The lesion involves the leg, an image taken at a distance — 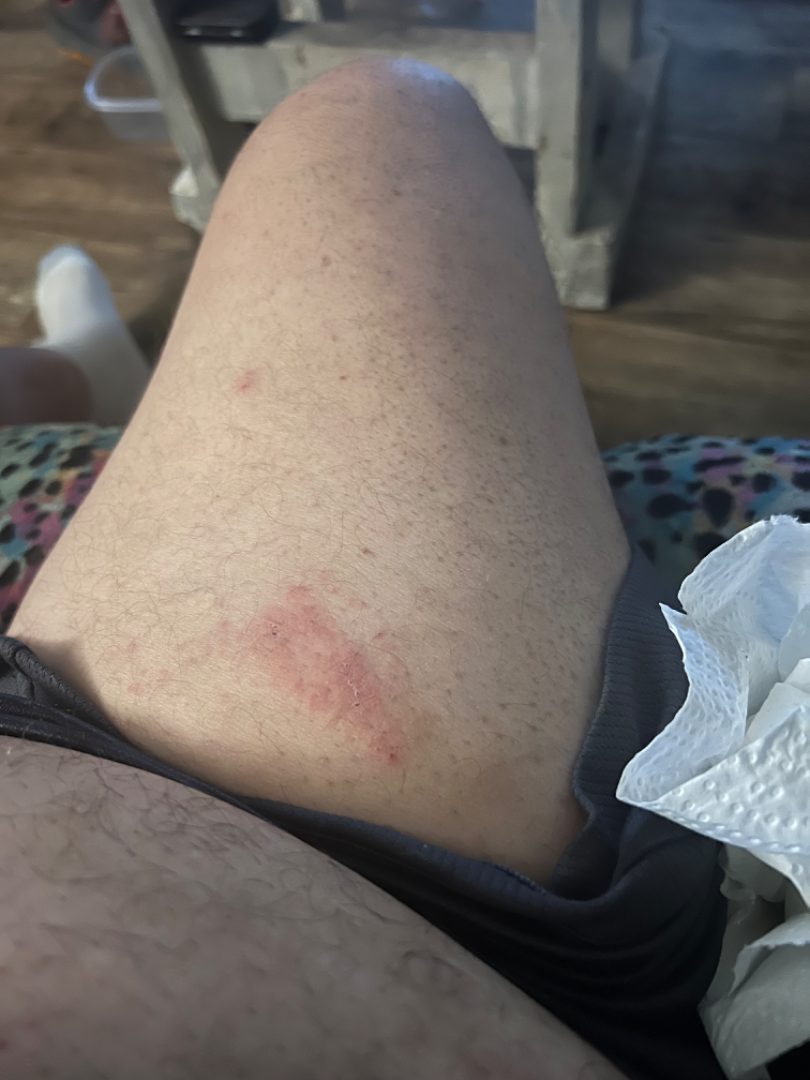Assessment:
The dermatologist could not determine a likely condition from the photograph alone.
Clinical context:
The contributor reports the lesion is raised or bumpy. No associated systemic symptoms reported. Self-categorized by the patient as a rash. Present for less than one week.